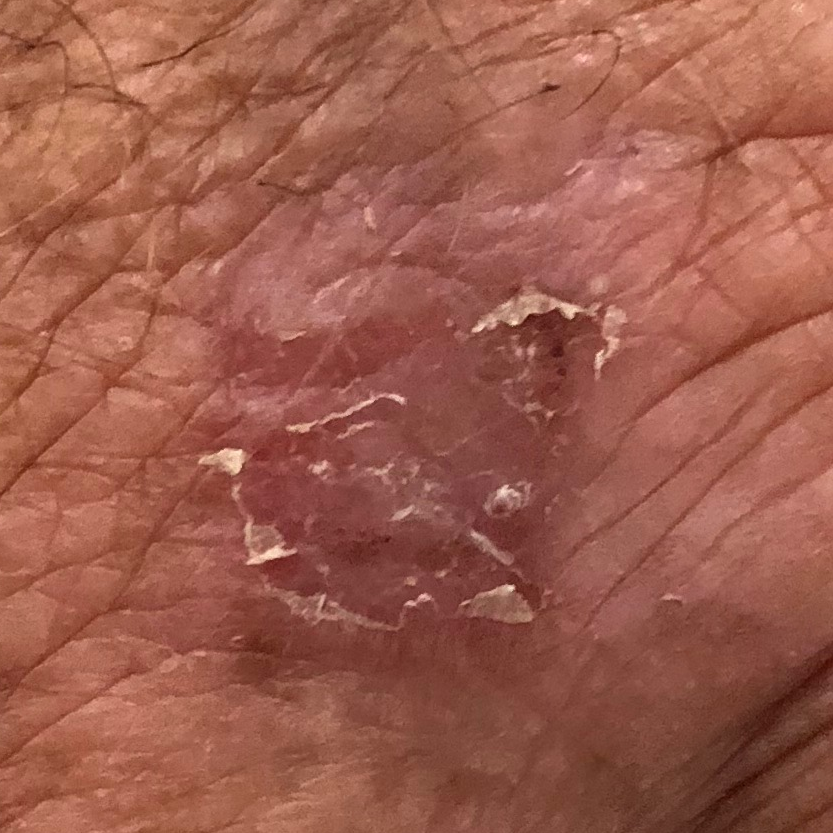A male subject 46 years of age. The chart notes prior malignancy (patient or family) and pesticide exposure. A clinical photograph showing a skin lesion. The lesion was found on an arm. Measuring about 8 × 2 mm. The patient describes that the lesion has not changed and does not itch. Histopathological examination showed an actinic keratosis.